A clinical photograph of a skin lesion.
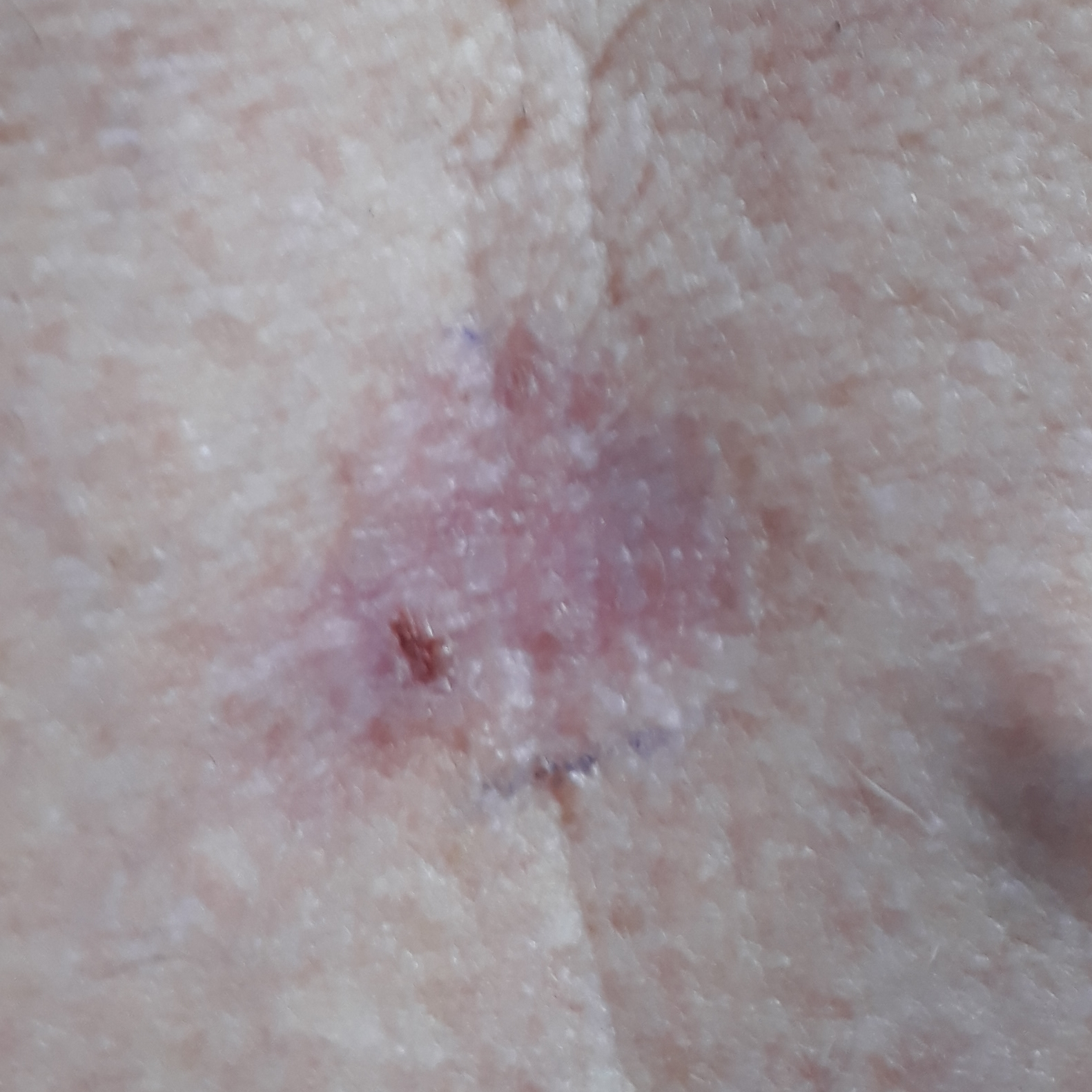Findings: The lesion involves the back. The lesion measures 15 × 10 mm. By the patient's account, the lesion hurts, but has not bled and has not changed. Conclusion: Biopsy-confirmed as a malignant skin lesion — a basal cell carcinoma.